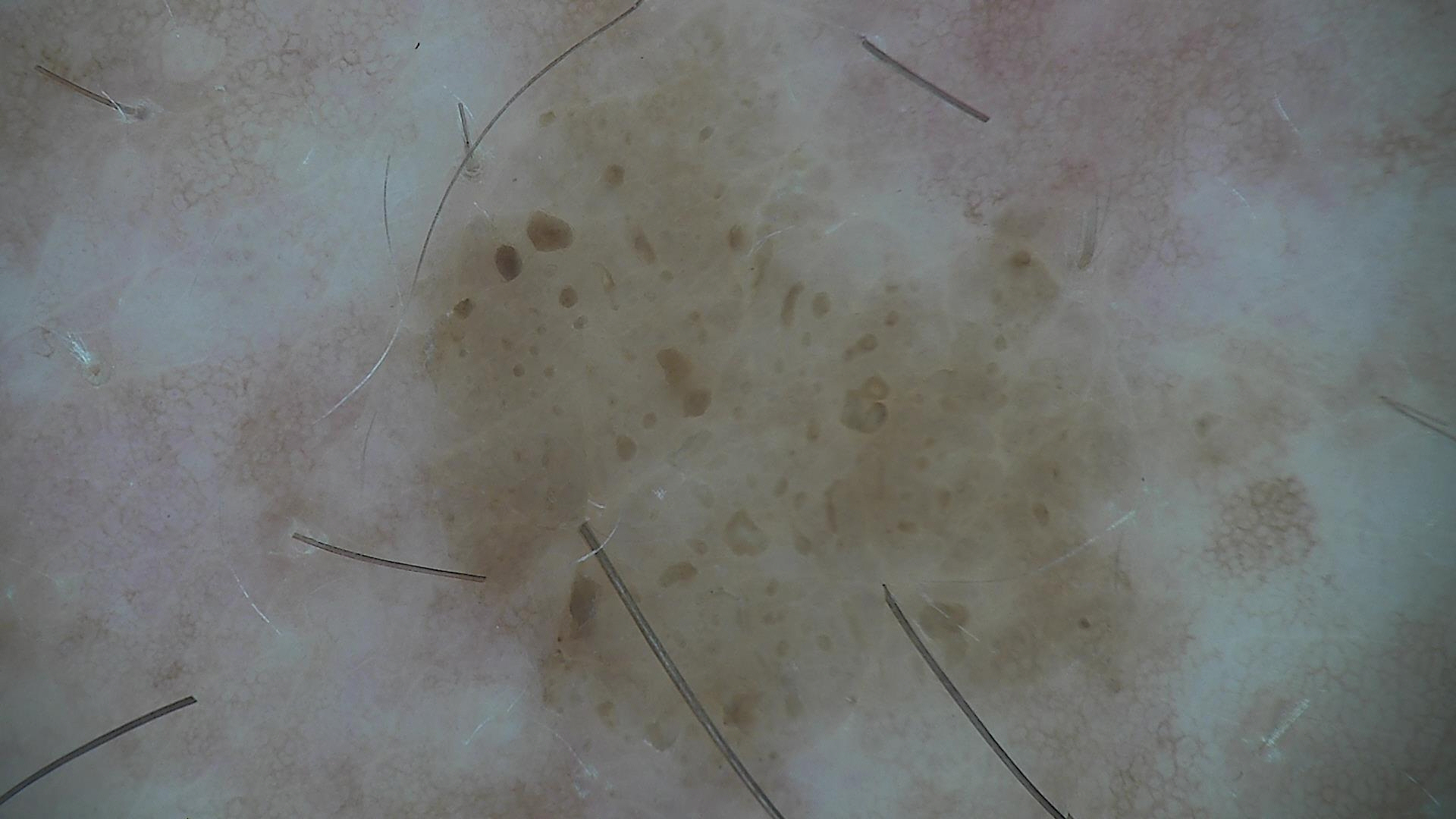A dermatoscopic image of a skin lesion. The morphology is that of a keratinocytic lesion. Classified as a benign lesion — a seborrheic keratosis.